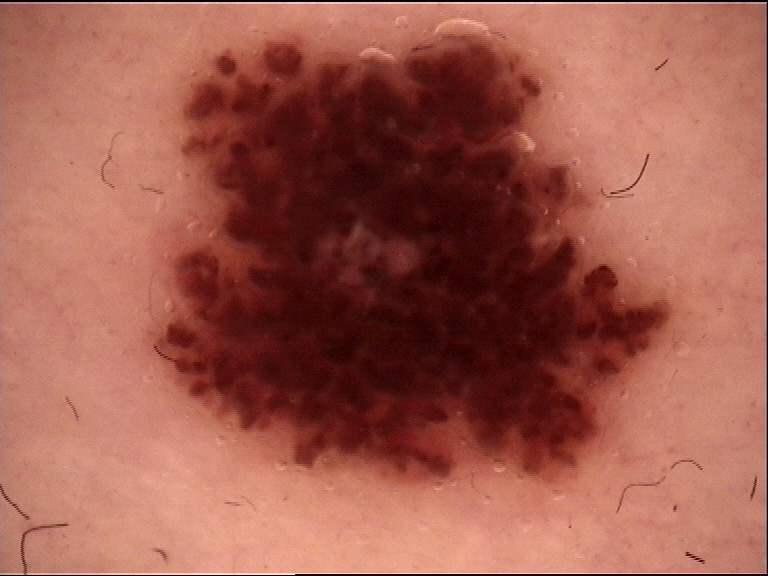{"diagnosis": {"name": "dysplastic compound nevus", "code": "cd", "malignancy": "benign", "super_class": "melanocytic", "confirmation": "expert consensus"}}